This image was taken at a distance: 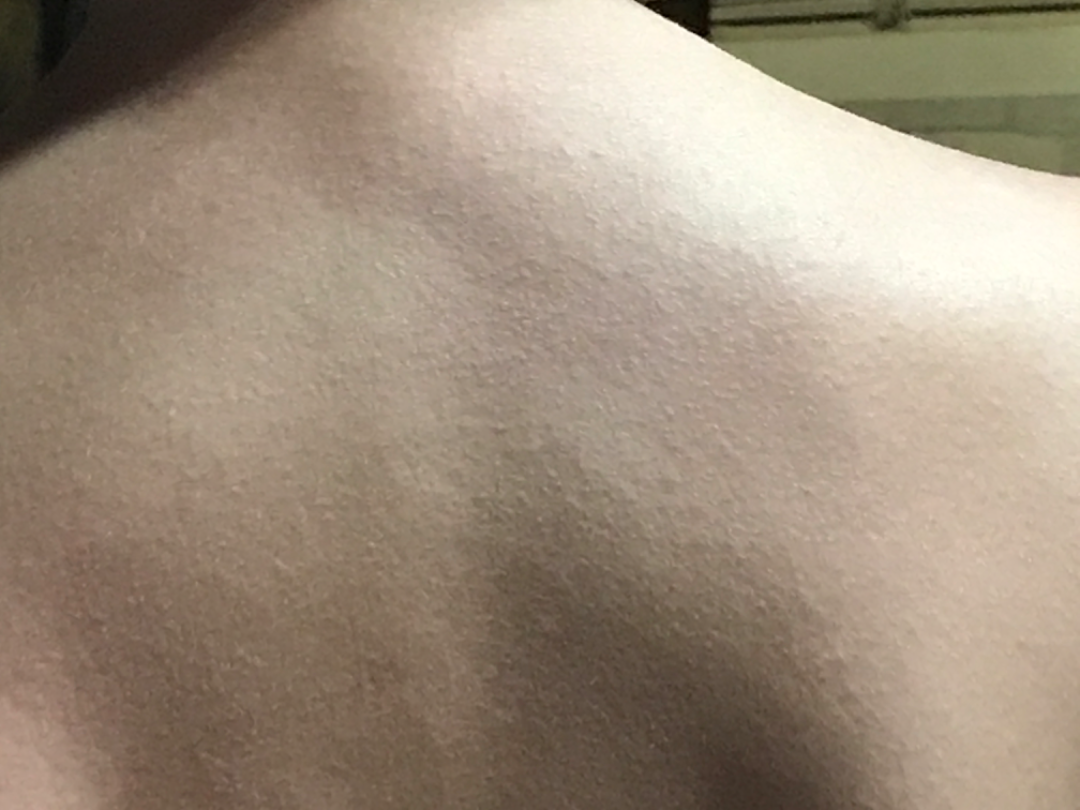differential:
  leading:
    - Miliaria